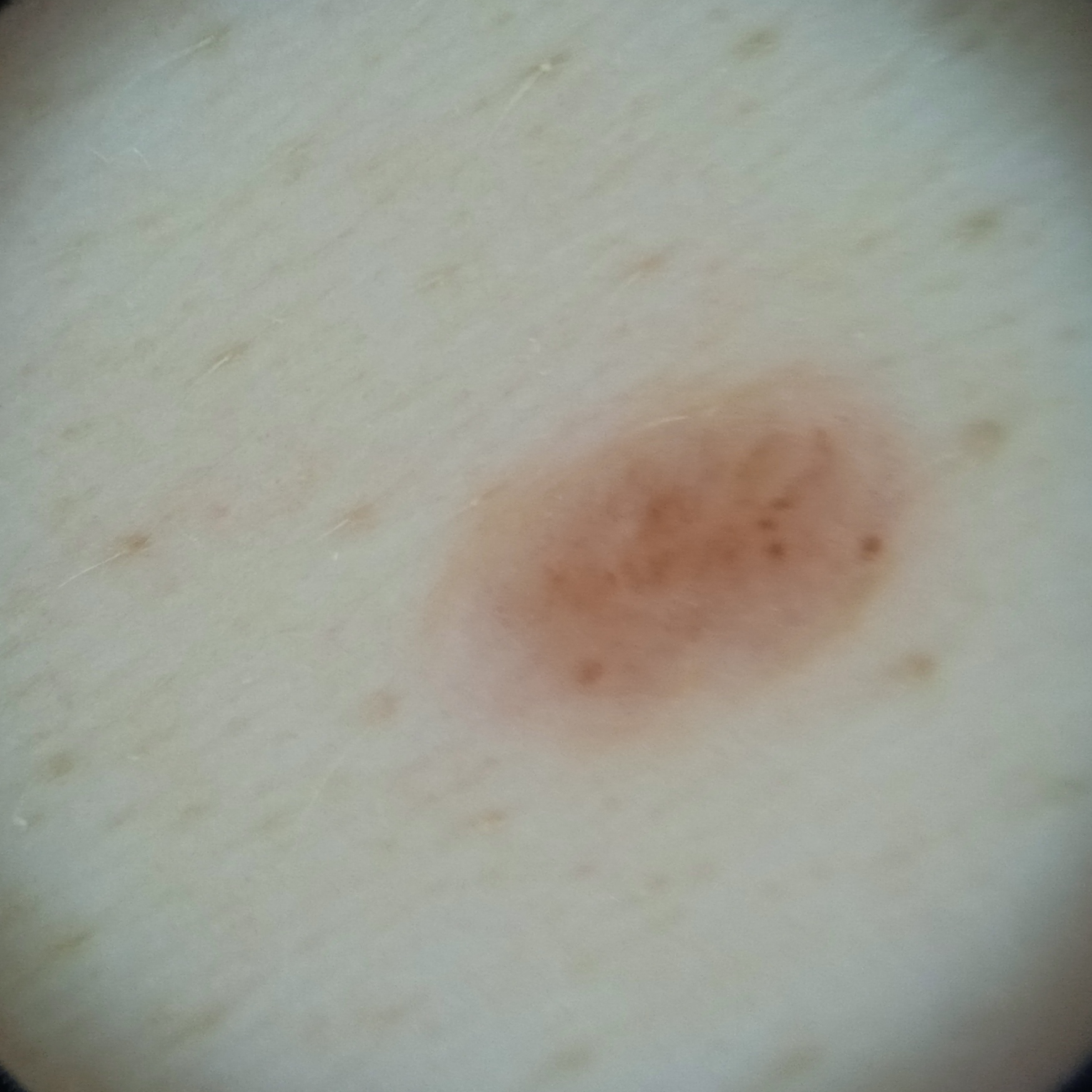referral context: research study (no referral diagnosis) | image: dermoscopic image | patient: female, 50 years old | site: the torso | size: 4.9 mm | assessment: melanocytic nevus (dermatologist consensus).